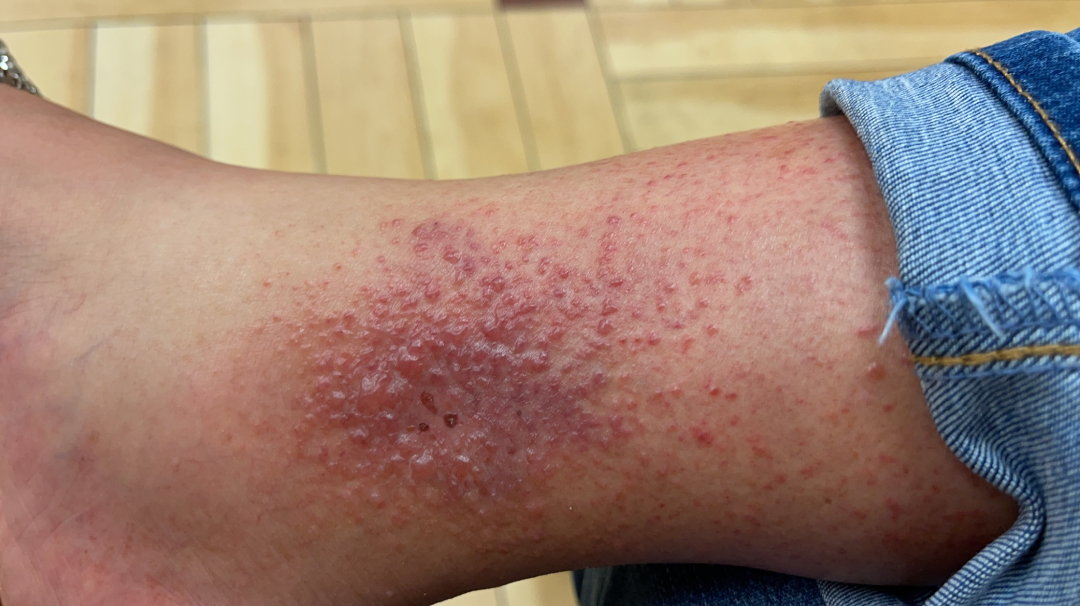The case was indeterminate on photographic review. This is a close-up image.